Dermoscopy of a skin lesion:
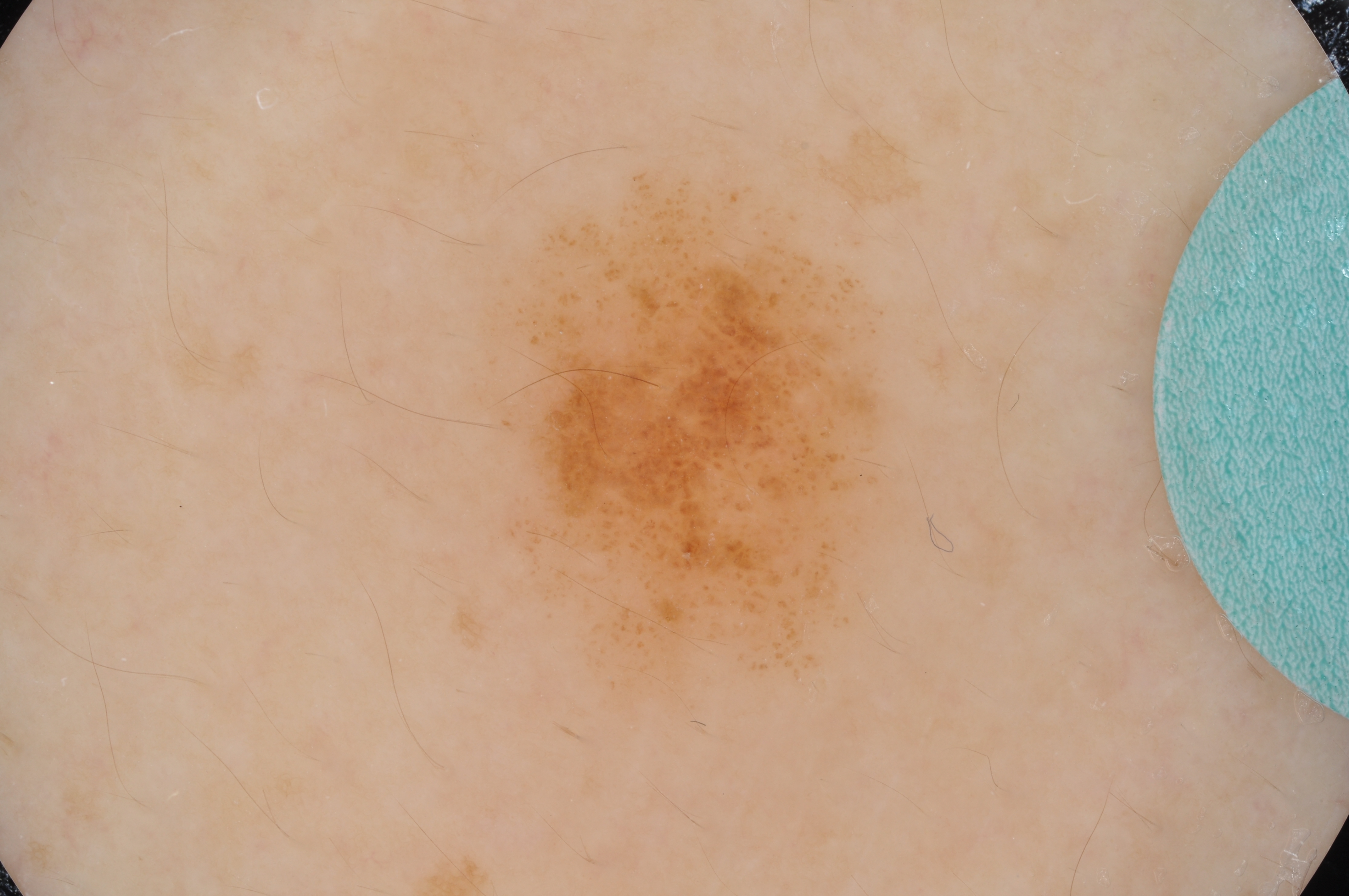{
  "lesion_extent": "moderate",
  "lesion_location": {
    "bbox_xyxy": [
      455,
      154,
      908,
      727
    ]
  },
  "diagnosis": {
    "malignancy": "benign",
    "provenance": "clinical"
  }
}